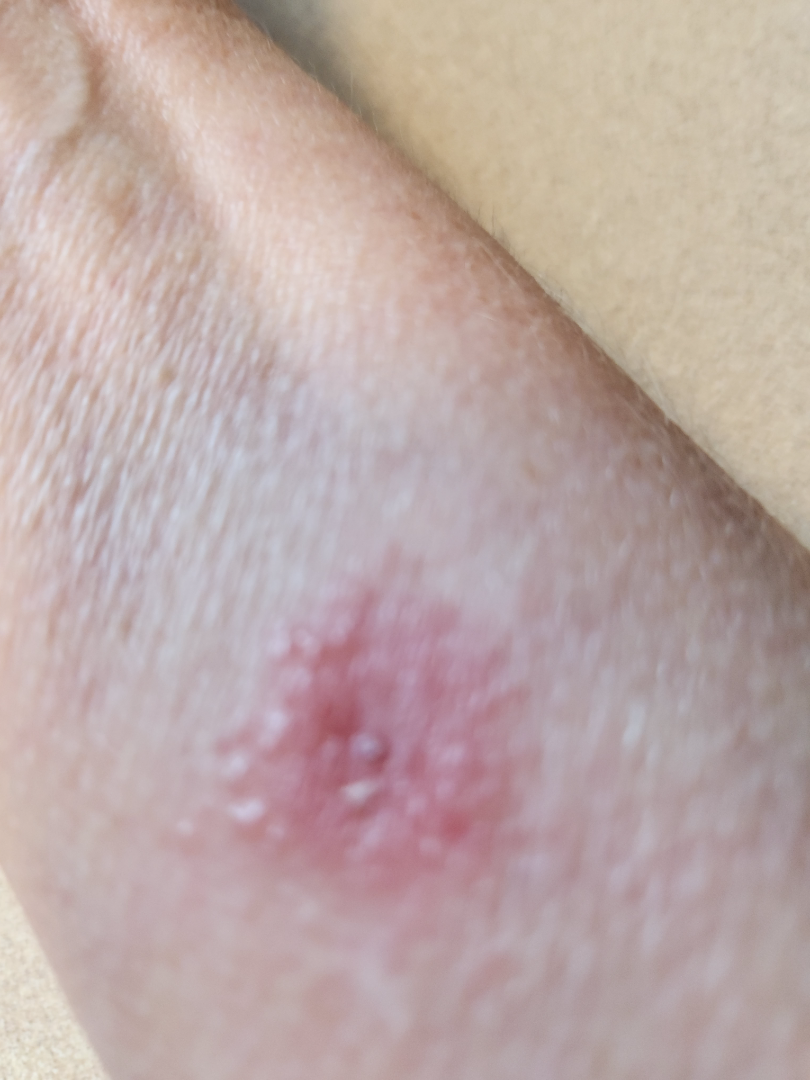The condition could not be reliably identified from the image.